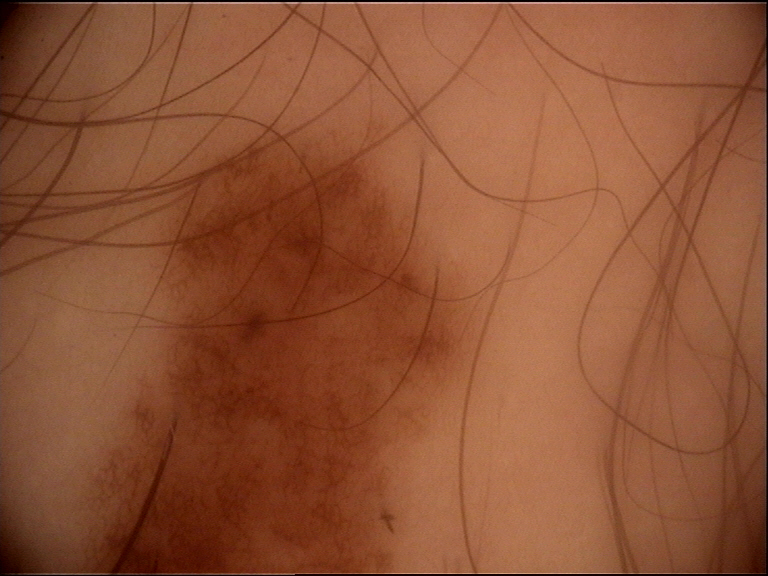Dermoscopy of a skin lesion. The diagnosis was a dysplastic junctional nevus.